History notes alcohol use, prior skin cancer (patient or family), and prior malignancy (patient or family). A male subject aged 53. A clinical photo of a skin lesion taken with a smartphone. The patient was assessed as skin type II:
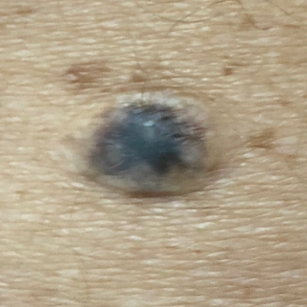The patient reports that the lesion is elevated.
The biopsy diagnosis was a benign skin lesion — a nevus.